A dermoscopy image of a single skin lesion.
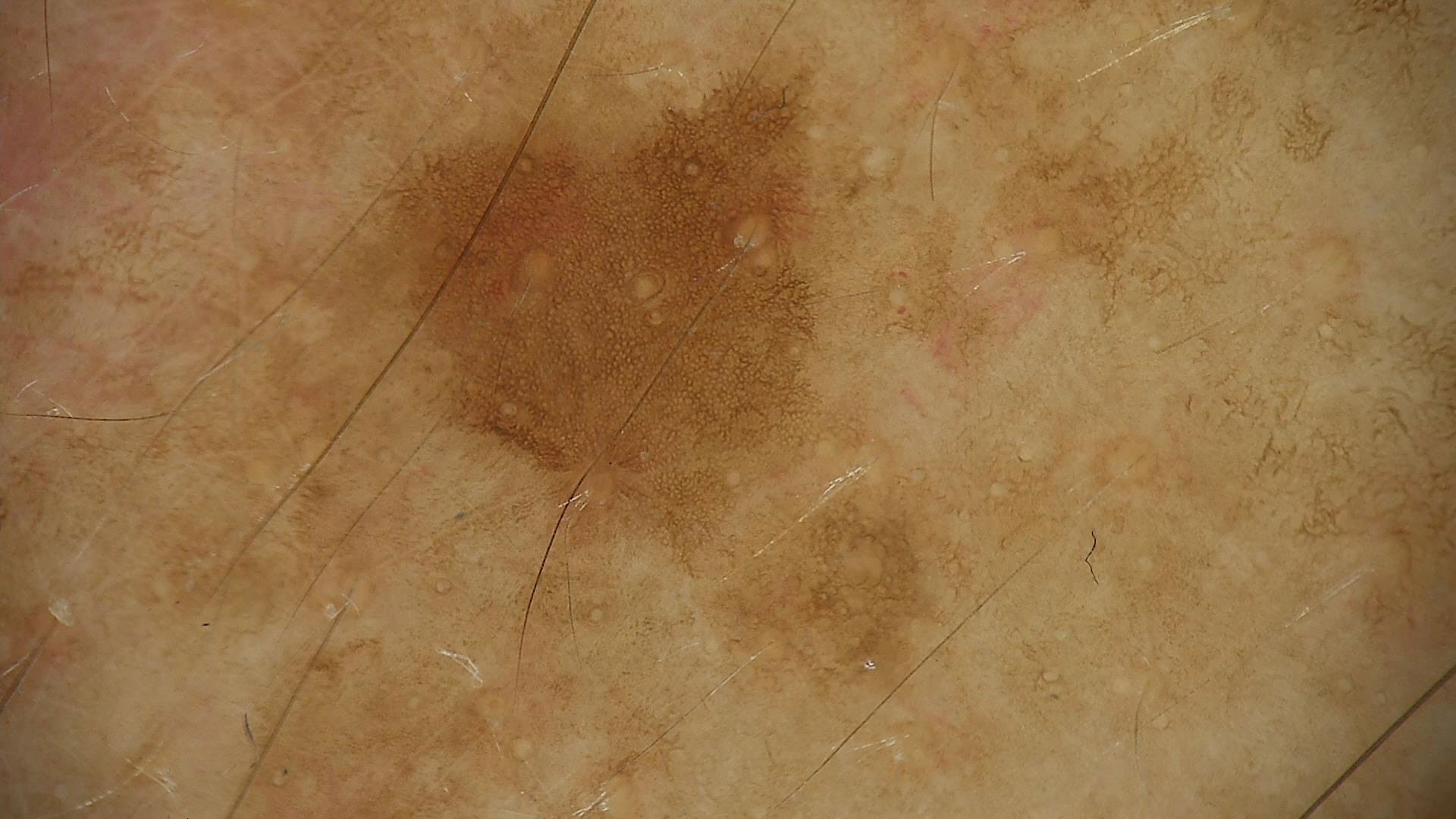The diagnostic label was a benign lesion — a solar lentigo.